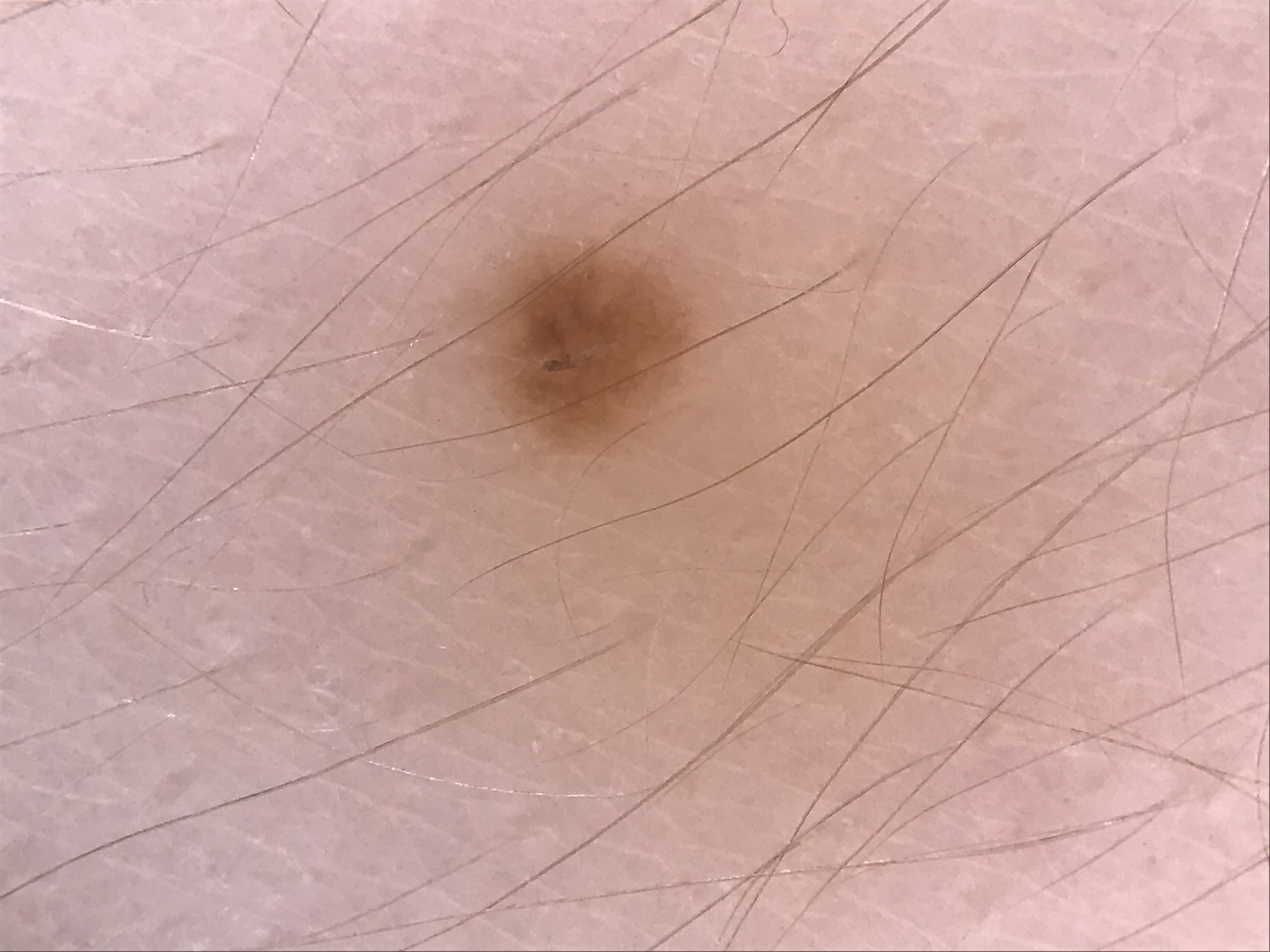Q: What was the diagnostic impression?
A: junctional nevus (expert consensus)